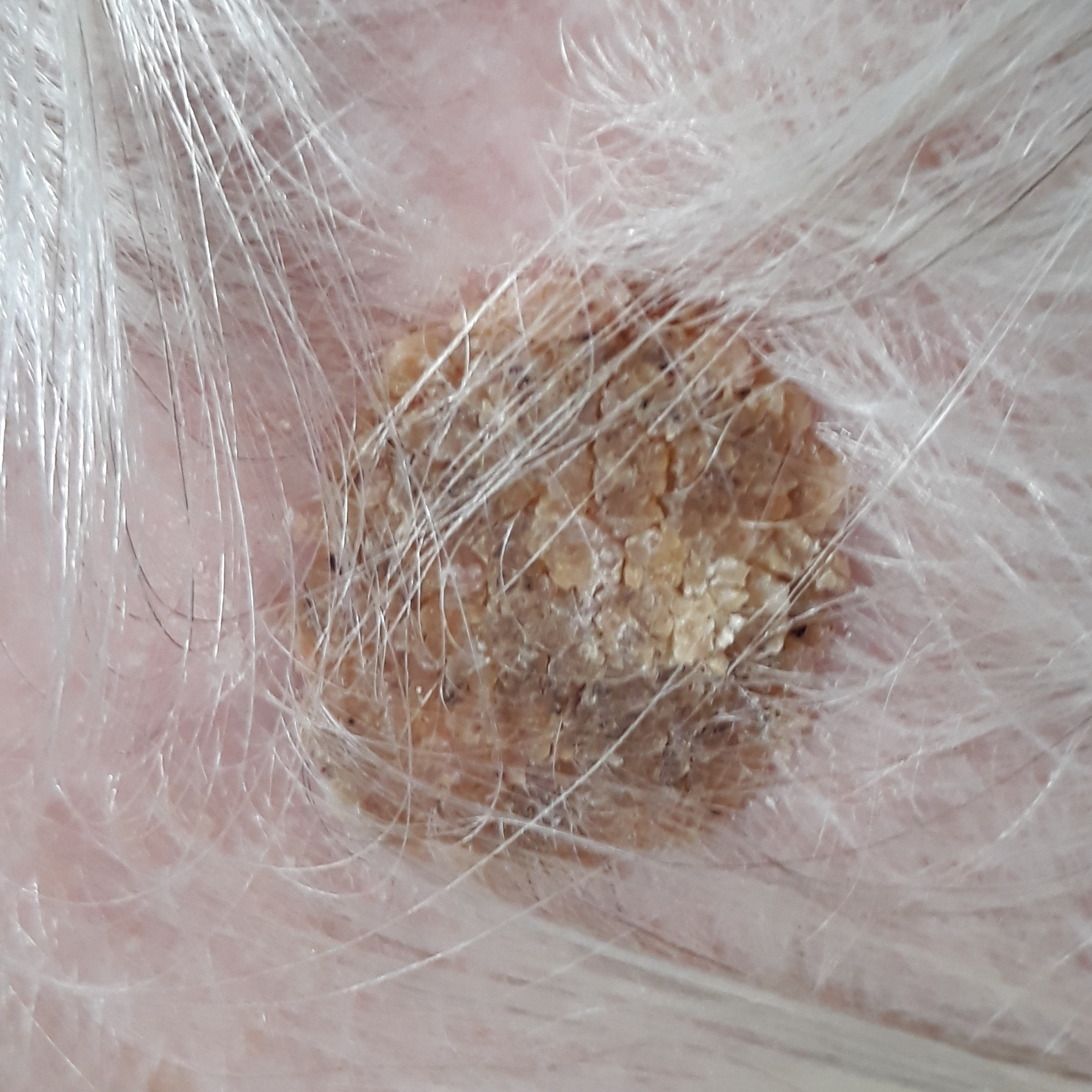The clinical impression was a seborrheic keratosis.